Recorded as Fitzpatrick phototype II; a clinical photograph showing a skin lesion; the chart notes pesticide exposure and prior skin cancer (patient or family) — 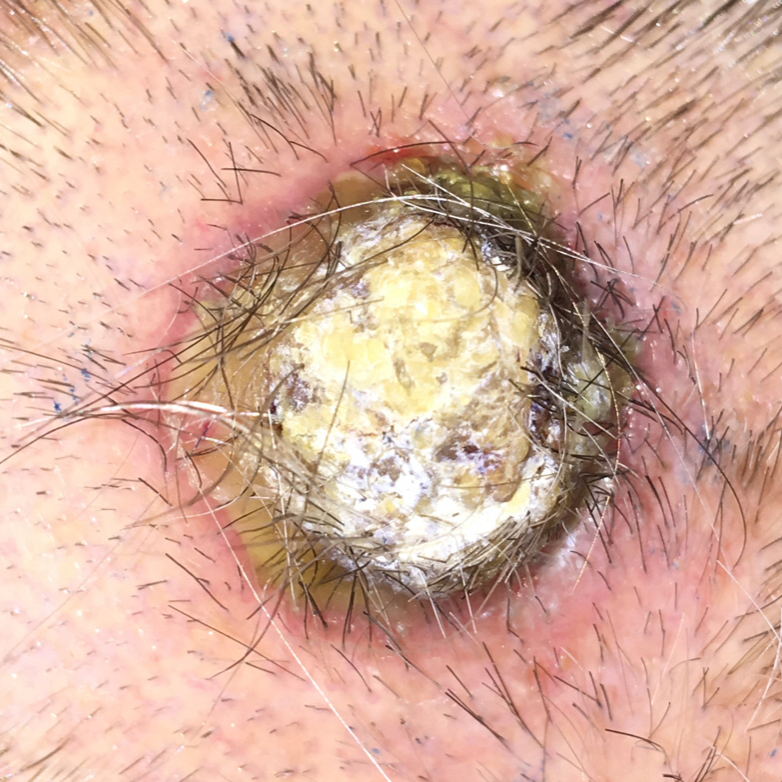Q: Where on the body is the lesion?
A: the scalp
Q: What are the lesion's dimensions?
A: approx. 30 × 25 mm
Q: Any reported symptoms?
A: elevation, itching
Q: What is this lesion?
A: squamous cell carcinoma (biopsy-proven)